This image was taken at an angle · the lesion involves the head or neck: 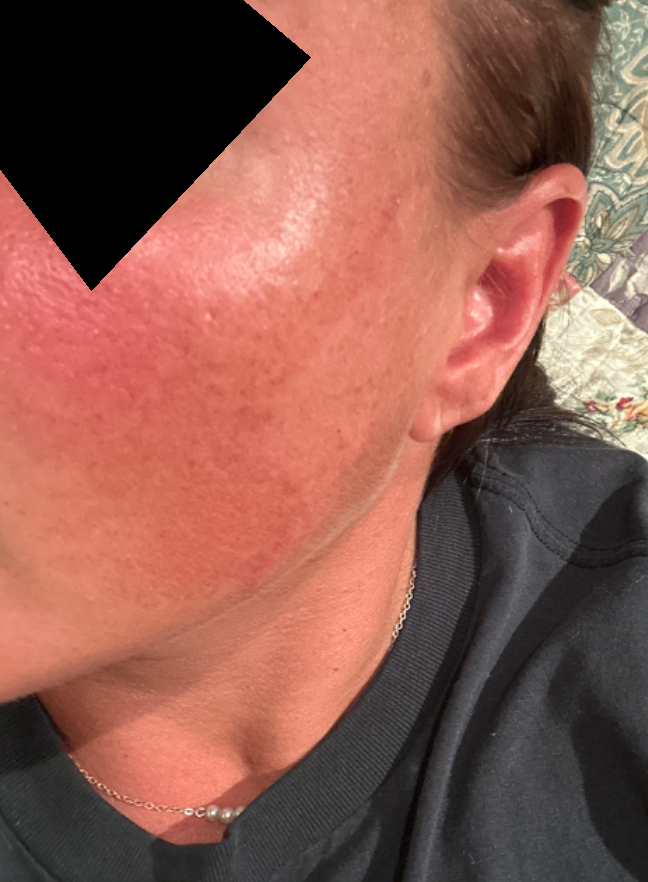Texture is reported as flat. The patient described the issue as a rash. On photographic review by a dermatologist, the impression on review was Melasma.